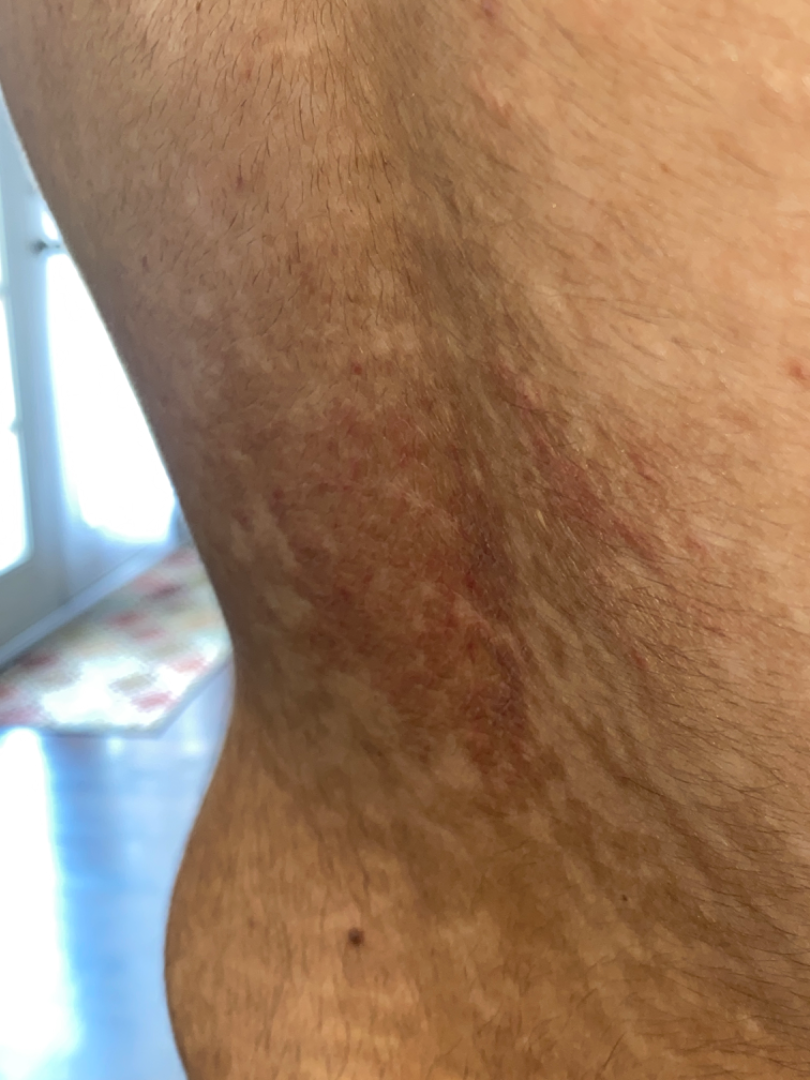Patient information: Texture is reported as rough or flaky. The photo was captured at an angle. Male contributor, age 18–29. The back of the torso is involved. The condition has been present for less than one week. The patient also reports mouth sores. The patient described the issue as a rash. The lesion is associated with enlargement, itching and bothersome appearance. Review: The favored diagnosis is Erythema ab igne; the differential also includes Livedo reticularis.